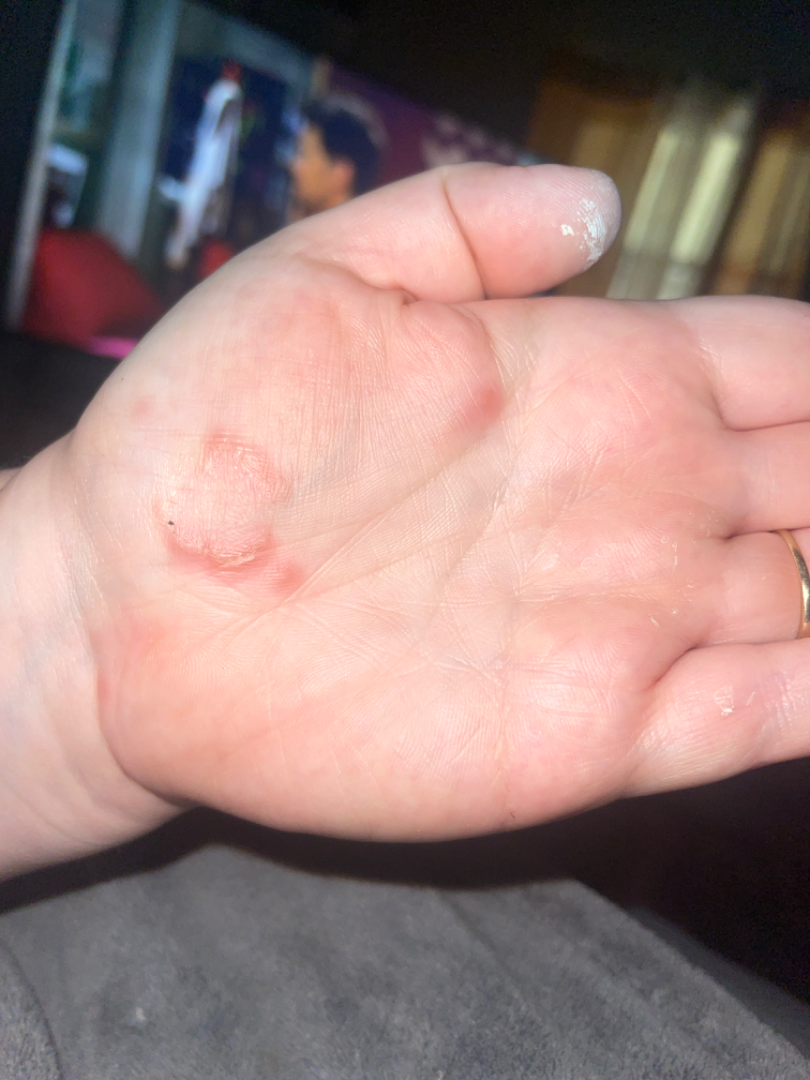Q: What was the assessment?
A: unable to determine
Q: What is the patient's skin tone?
A: human graders estimated 2 on the MST
Q: Duration?
A: one to four weeks
Q: Constitutional symptoms?
A: none reported
Q: How does the patient describe it?
A: skin that appeared healthy to them
Q: Image view?
A: close-up
Q: Where on the body?
A: palm
Q: What symptoms does the patient report?
A: pain and itching